The photograph was taken at an angle:
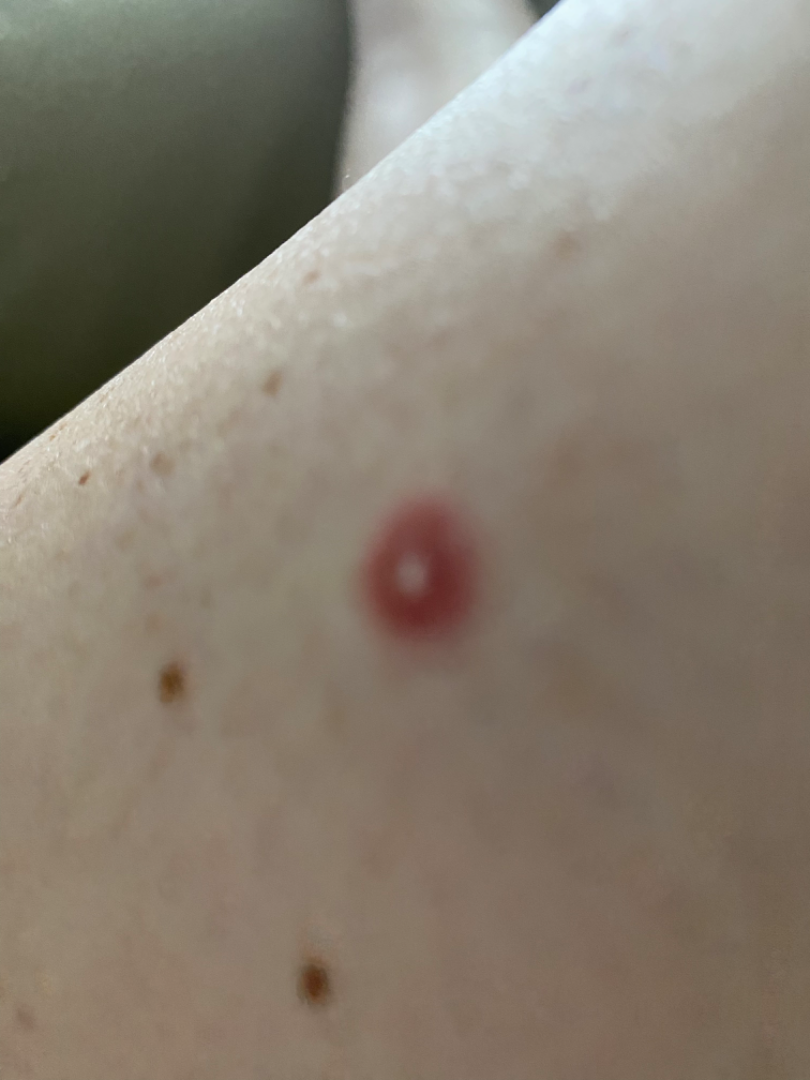Findings:
The dermatologist could not determine a likely condition from the photograph alone.